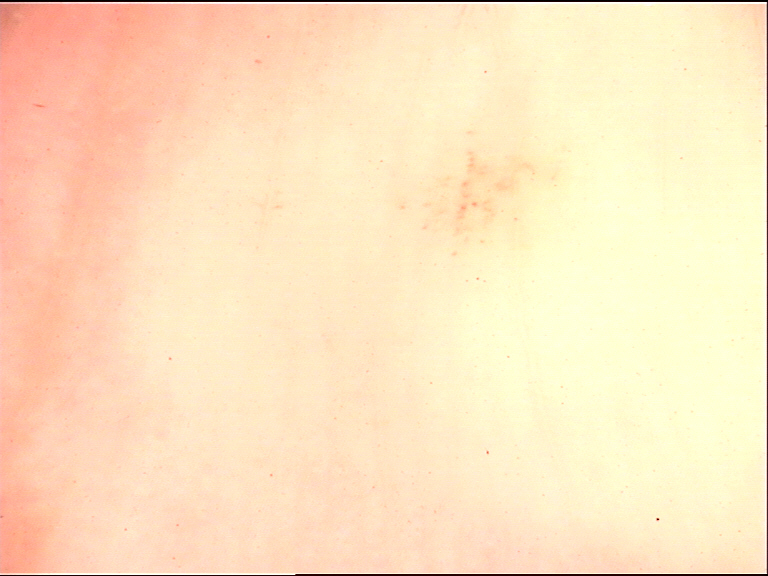Q: What kind of image is this?
A: dermoscopy
Q: What was the diagnostic impression?
A: acral junctional nevus (expert consensus)